A dermoscopic image of a skin lesion.
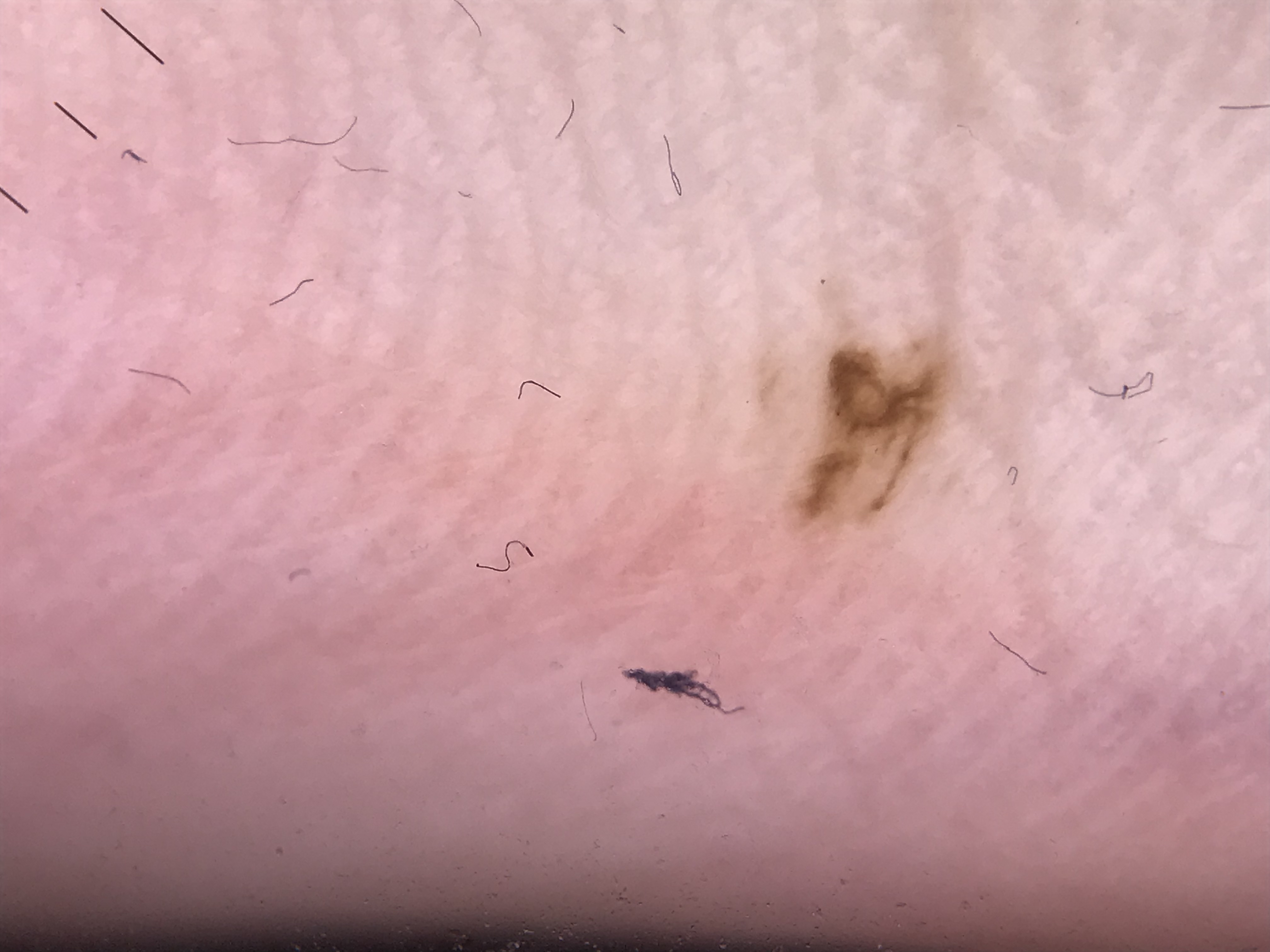Q: What is this lesion?
A: acral junctional nevus (expert consensus)